A skin lesion imaged with a dermatoscope · the subject is a male aged approximately 45: 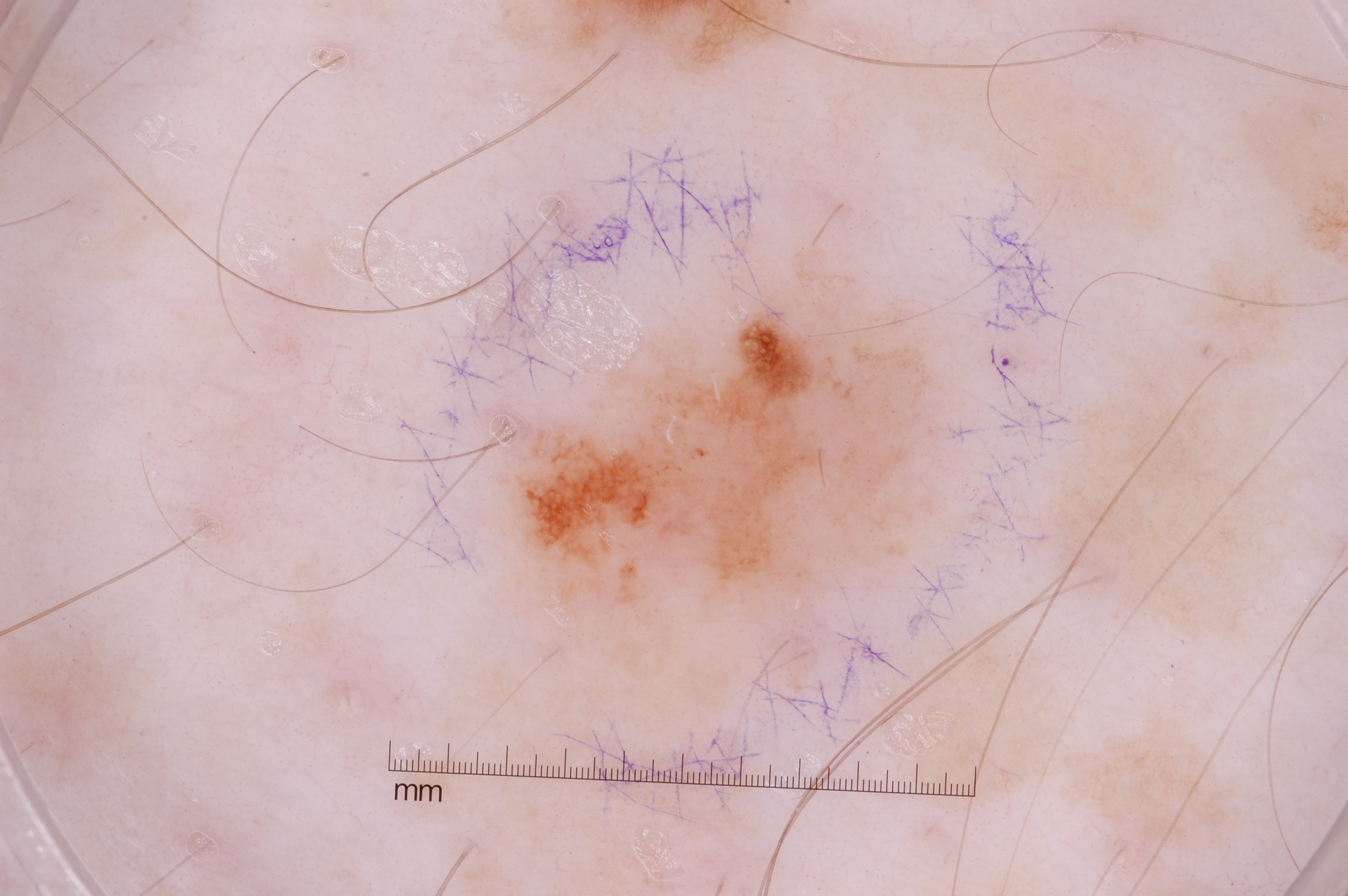The lesion covers approximately 9% of the dermoscopic field.
With coordinates (x1, y1, x2, y2), the lesion spans [506, 273, 937, 630].
On dermoscopy, the lesion shows no negative network, milia-like cysts, pigment network, or streaks.
Clinically diagnosed as a melanocytic nevus.